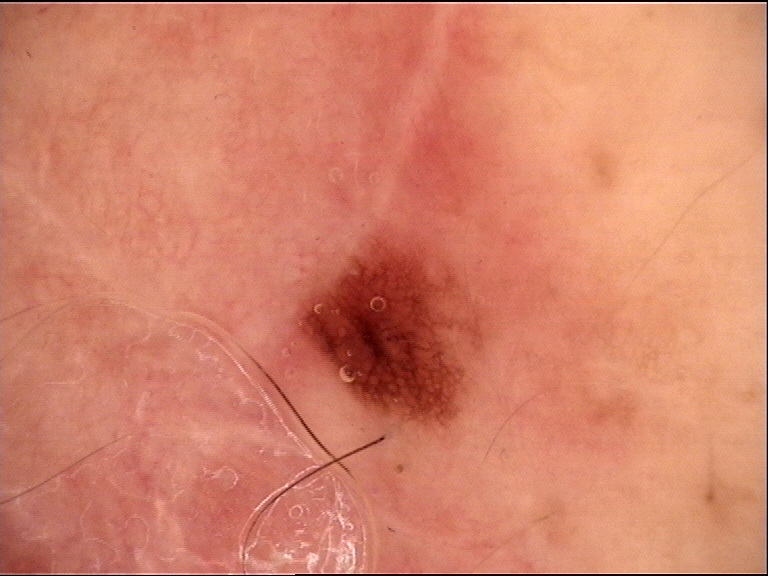{"image": "dermoscopy", "diagnosis": {"name": "dysplastic junctional nevus", "code": "jd", "malignancy": "benign", "super_class": "melanocytic", "confirmation": "expert consensus"}}